A clinical photo of a skin lesion taken with a smartphone · a patient in their mid-80s — 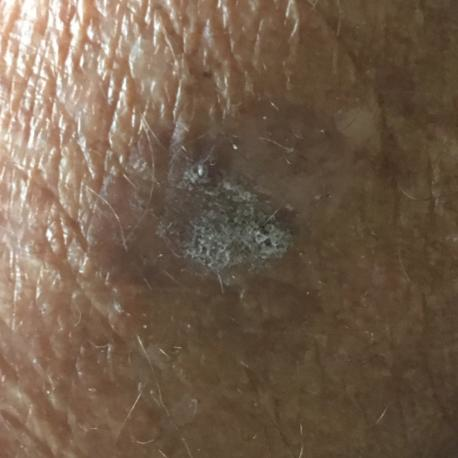Findings:
* region · an arm
* reported symptoms · elevation, itching
* diagnosis · seborrheic keratosis (clinical consensus)